Dermoscopy of a skin lesion. A male subject, aged approximately 80 — 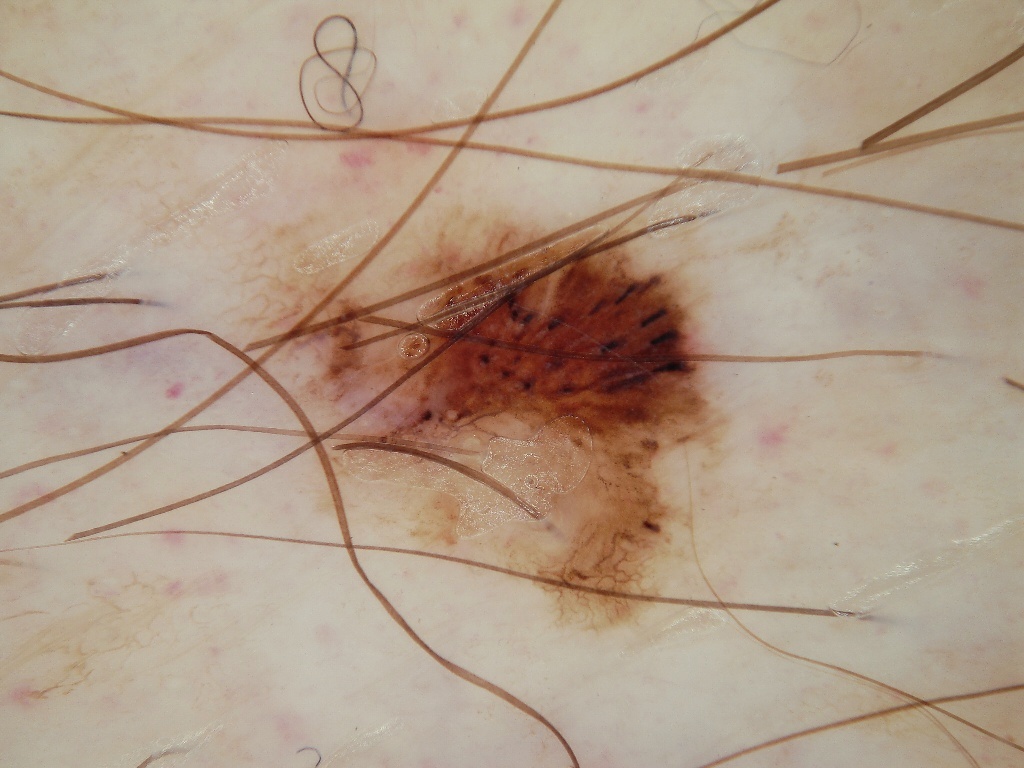Case summary: Dermoscopically, the lesion shows pigment network, globules, and streaks; no negative network or milia-like cysts. A mid-sized lesion within the field. With coordinates (x1, y1, x2, y2), the lesion occupies the region 184/191/740/646. Conclusion: On biopsy, the diagnosis was a melanoma.